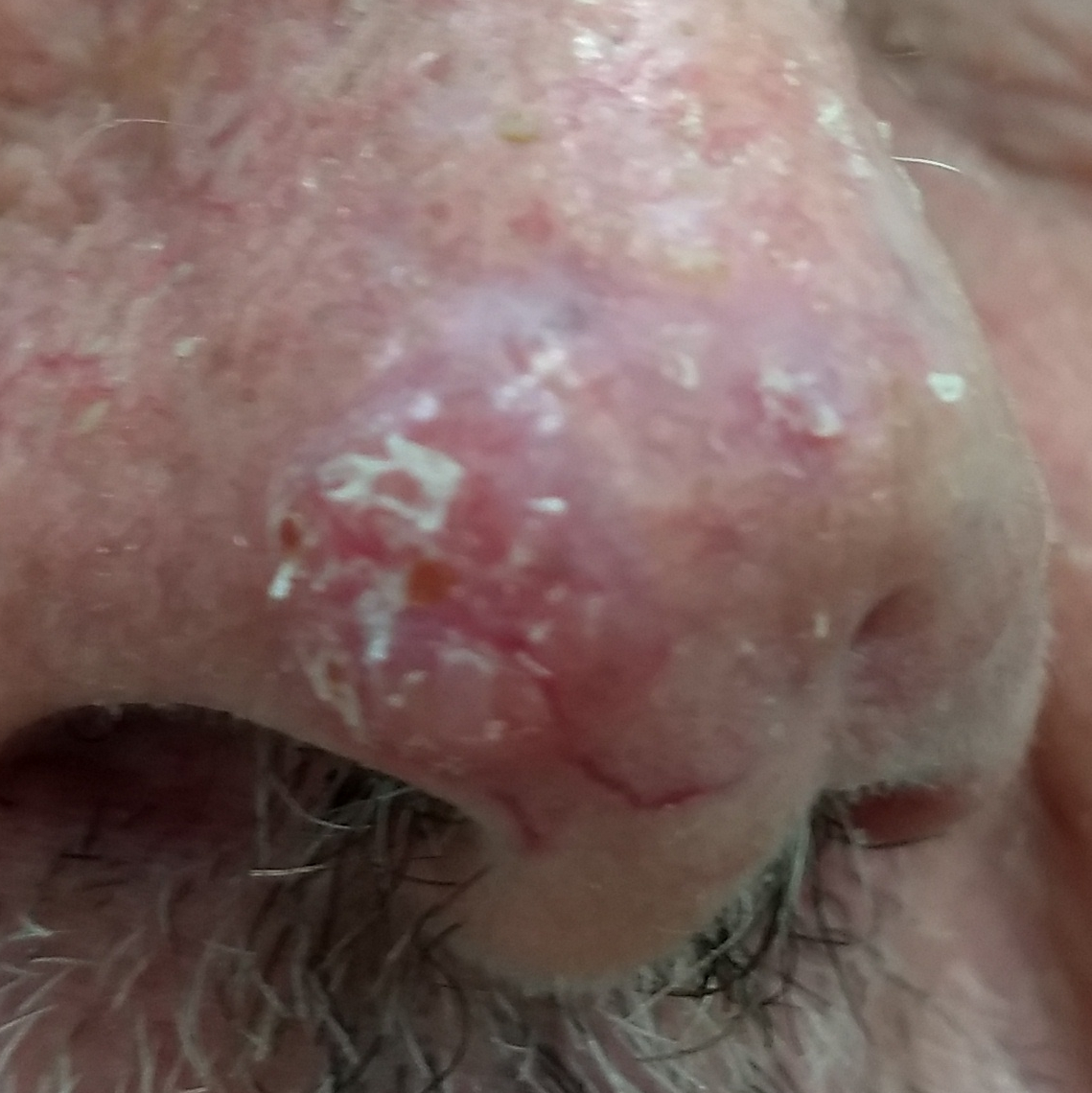– risk factors — pesticide exposure, no tobacco use
– image type — smartphone clinical photo
– subject — male, 71 years of age
– skin phototype — III
– anatomic site — the nose
– symptoms — elevation, itching / no pain, no bleeding
– diagnosis — basal cell carcinoma (biopsy-proven)